A female patient 20 years of age · a dermatoscopic image of a skin lesion · acquired for a research image collection, with no referral diagnosis.
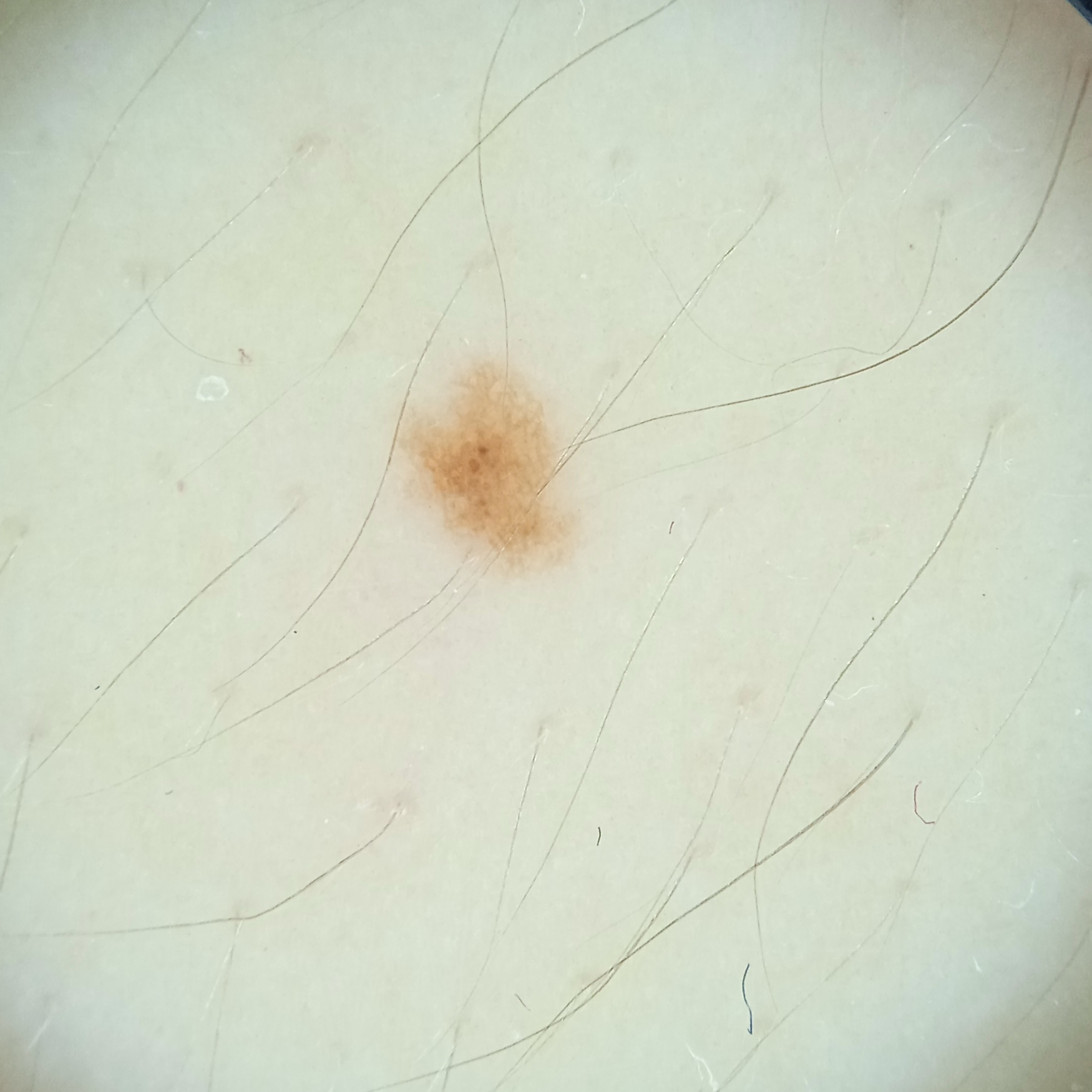Q: Where is the lesion?
A: an arm
Q: Lesion size?
A: 2.5 mm
Q: What was the diagnosis?
A: melanocytic nevus (dermatologist consensus)